A dermatoscopic image of a skin lesion: 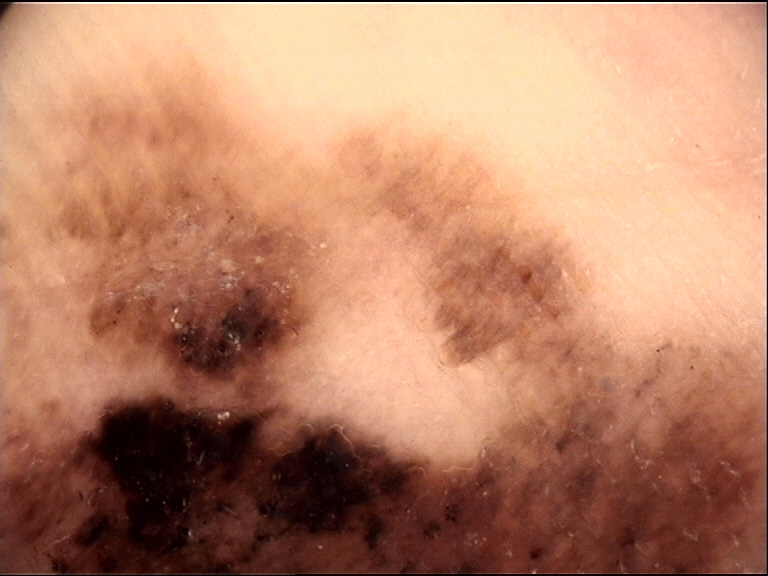Diagnosis: Histopathology confirmed a malignancy — an acral lentiginous melanoma.